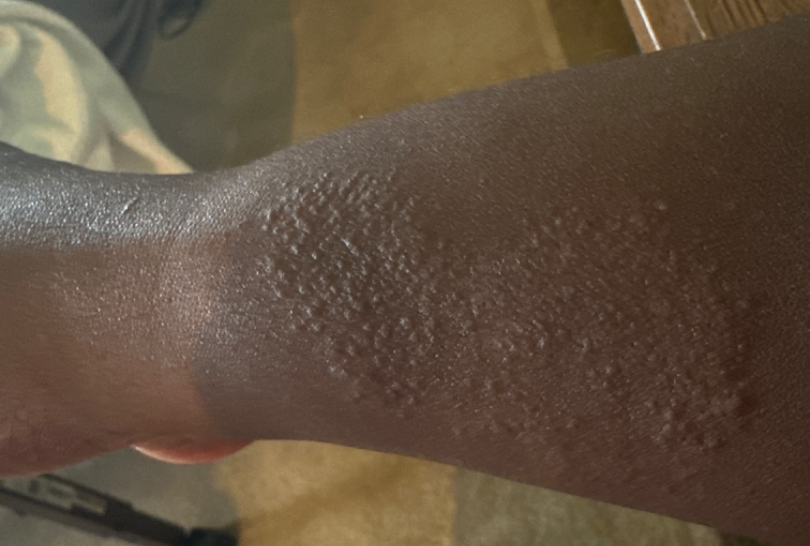Review:
The reviewer was unable to grade this case for skin condition.
Patient information:
The affected area is the arm. The patient described the issue as a rash. Non-clinician graders estimated MST 6 or 8. Symptoms reported: itching and bothersome appearance. The photograph is a close-up of the affected area. The patient reports the condition has been present for three to twelve months. The patient reported no systemic symptoms. The lesion is described as rough or flaky and raised or bumpy.